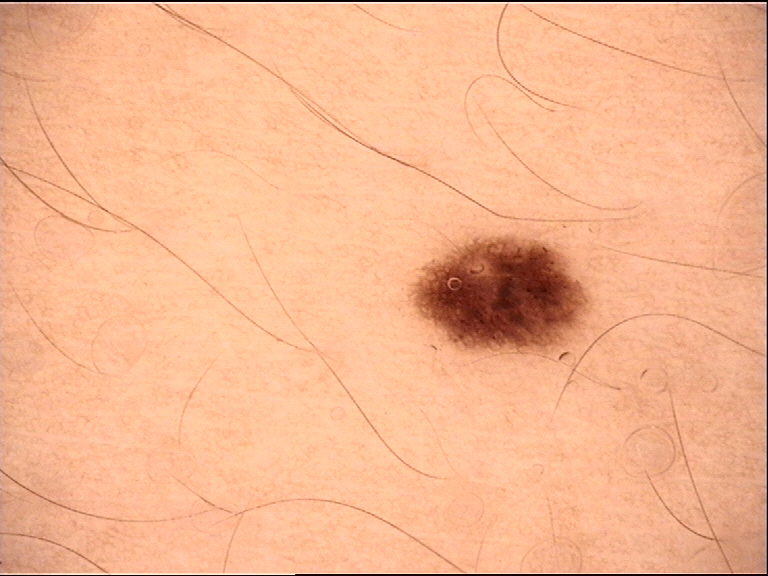class: dysplastic junctional nevus (expert consensus).